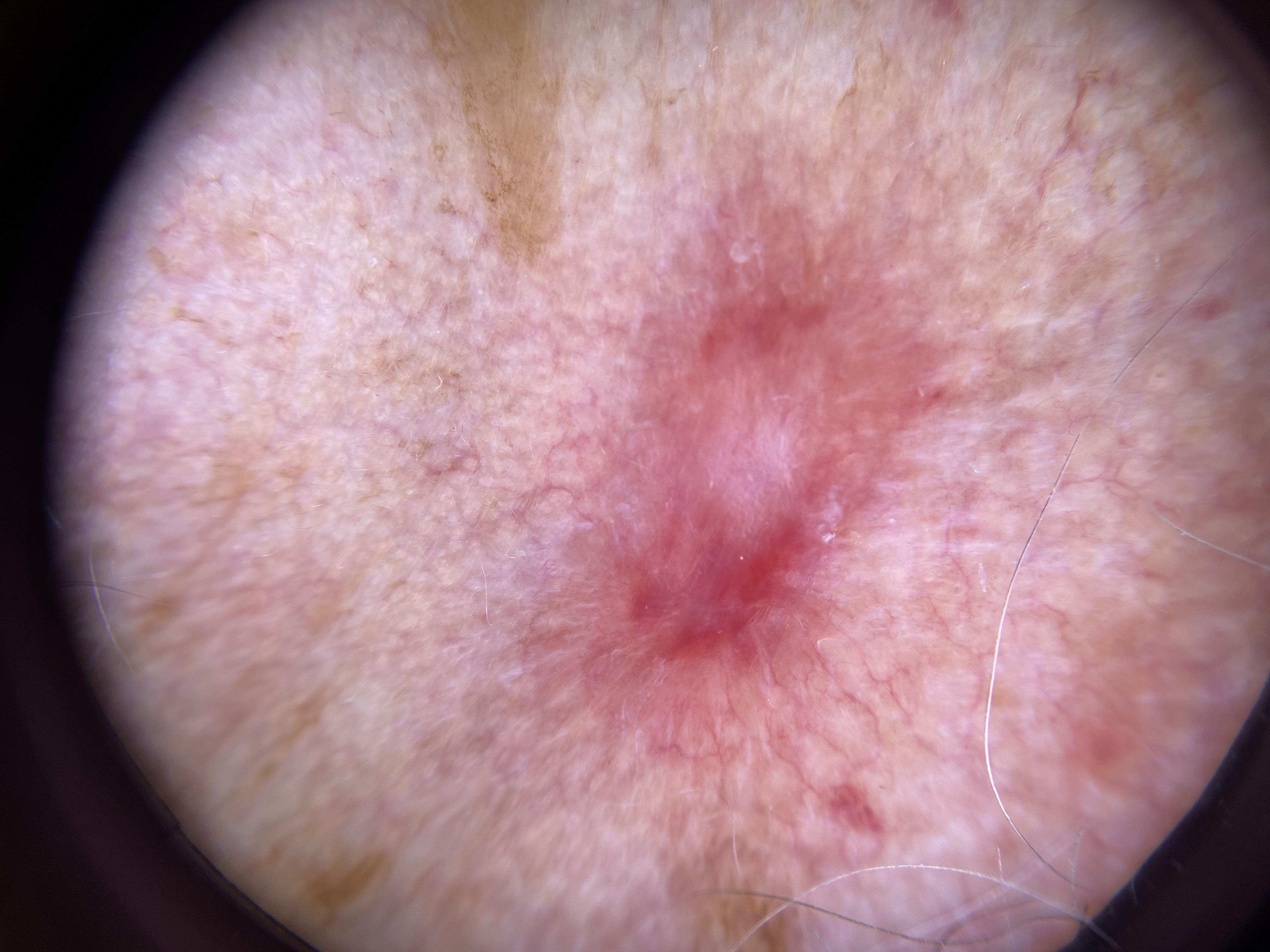diagnostic label: Squamous cell carcinoma (biopsy-proven).